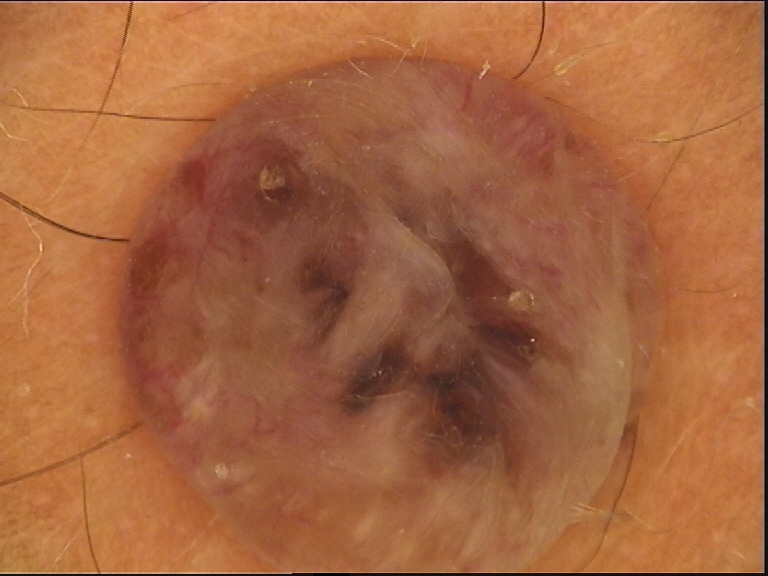A dermatoscopic image of a skin lesion.
This is a banal lesion.
Diagnosed as a dermal nevus.